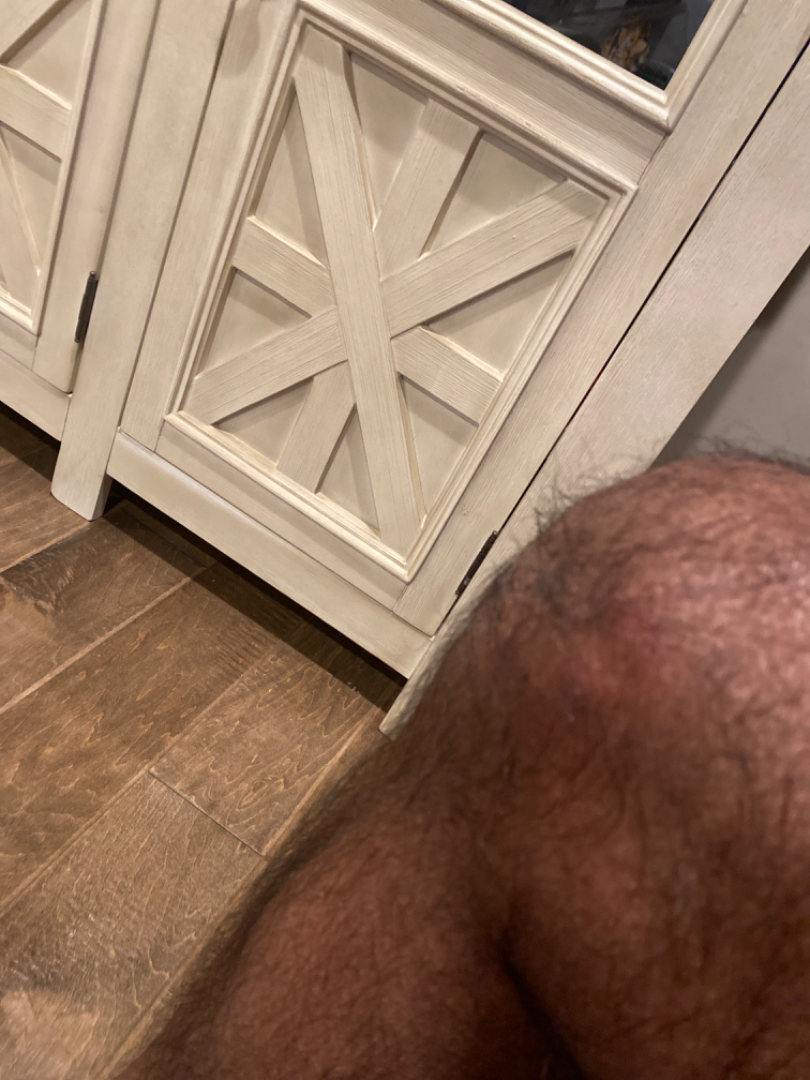Review: The reviewing dermatologist was unable to assign a differential diagnosis from the image. Patient information: Texture is reported as raised or bumpy and fluid-filled. The affected area is the leg. The condition has been present for less than one week. This image was taken at a distance.